Reported duration is about one day · self-categorized by the patient as skin that appeared healthy to them · the lesion is described as fluid-filled · the affected area is the leg · this image was taken at an angle:
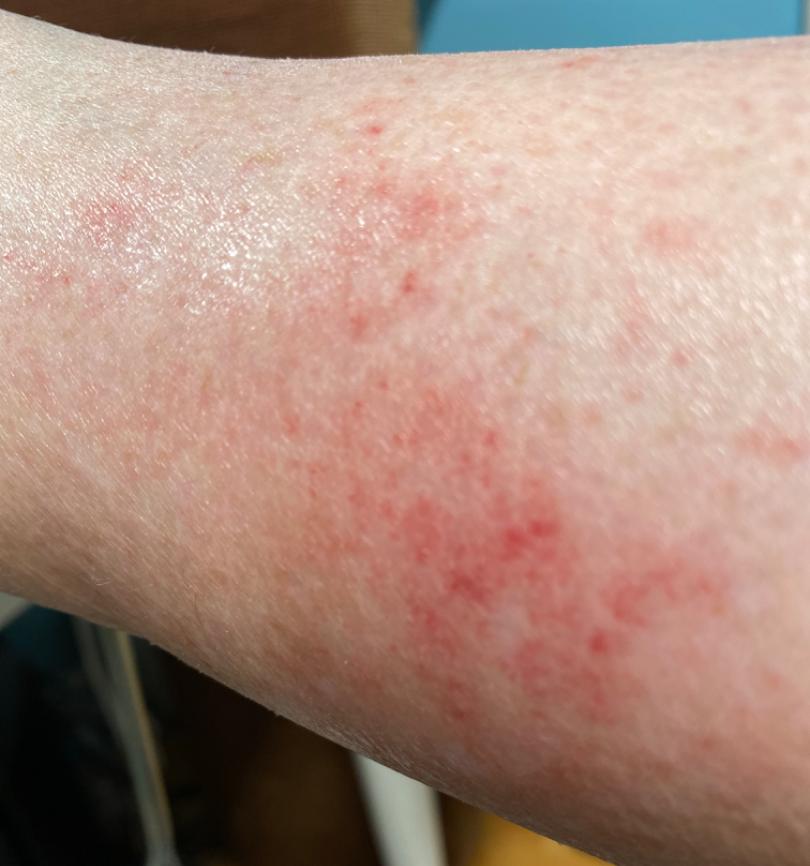assessment: ungradable on photographic review